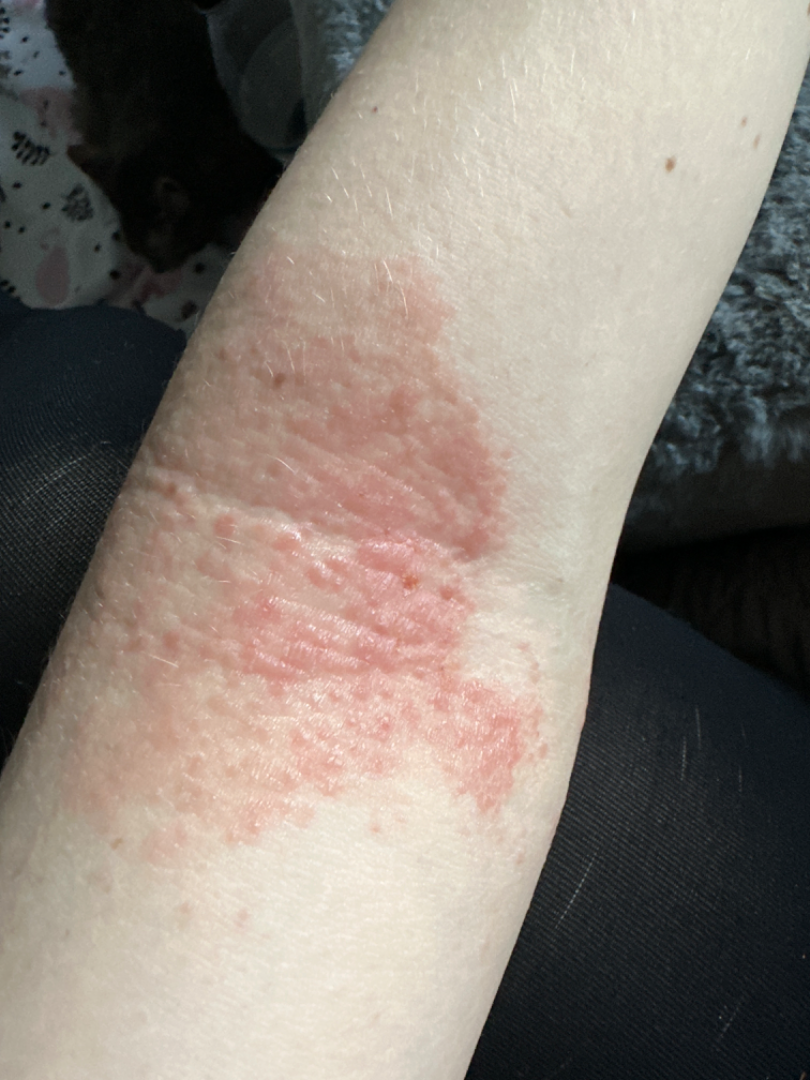  patient: female, age 30–39
  shot_type: close-up
  body_site: arm
  differential:
    leading:
      - Eczema
    unlikely:
      - Tinea
      - Allergic Contact Dermatitis